The affected area is the front of the torso and leg; a close-up photograph; male patient, age 40–49:
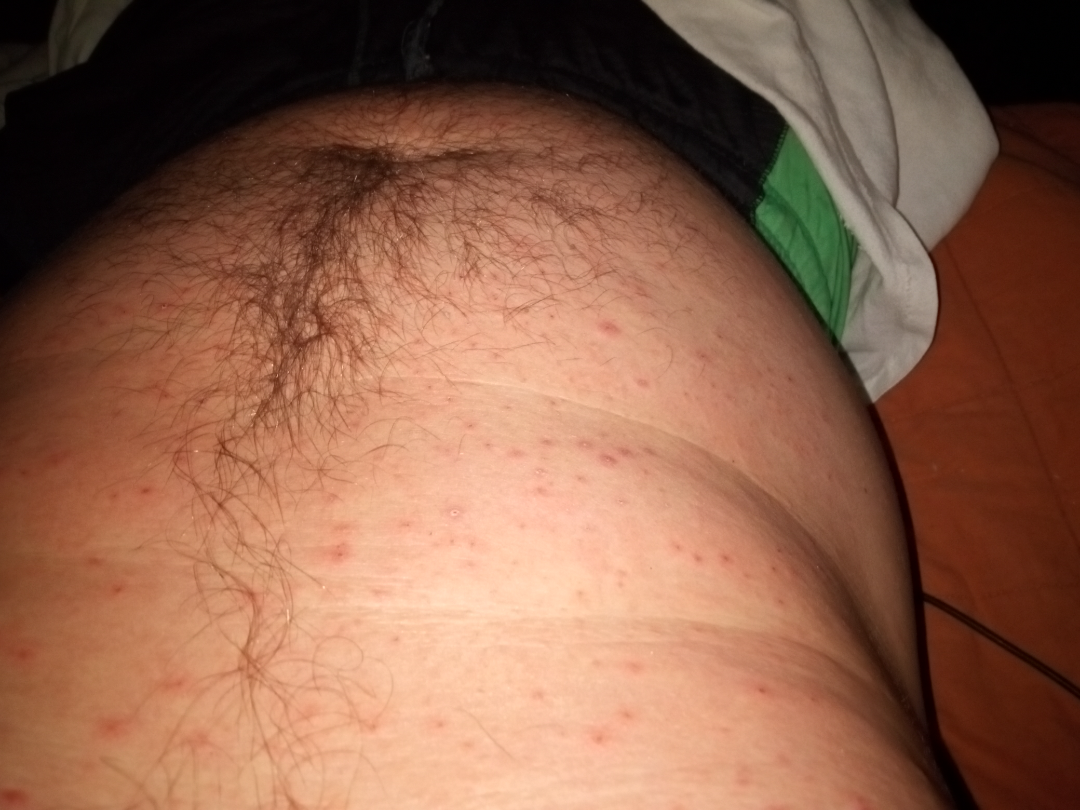Assessment:
The reviewing dermatologists' impression was: Scabies (0.29); Grover's disease (0.18); Folliculitis (0.15); Drug Rash (0.15); Syphilis (0.11); Pityriasis lichenoides (0.11).